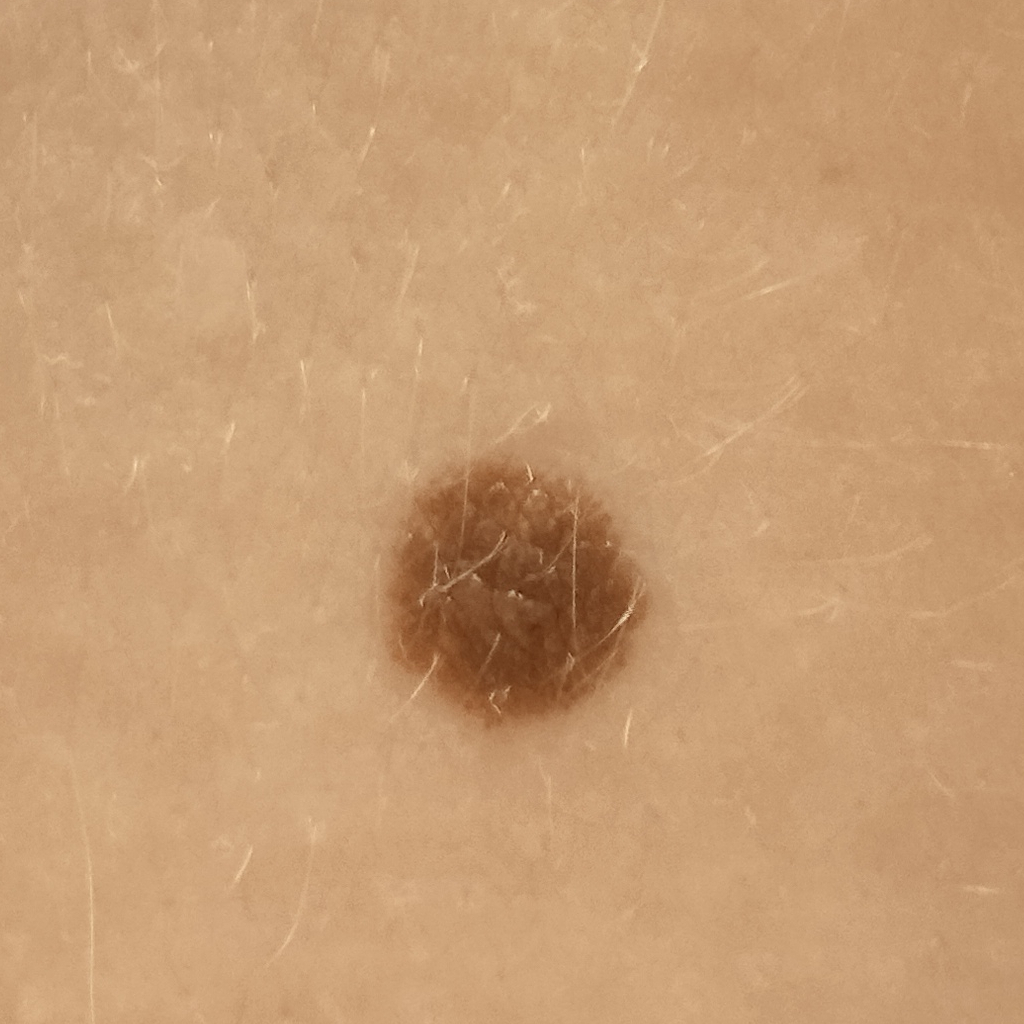risk_factors:
  positive:
    - a history of sunbed use
referral: research study (no referral diagnosis)
sun_reaction: skin reddens with sun exposure
image: clinical photograph
lesion_size:
  diameter_mm: 9.1
diagnosis:
  name: melanocytic nevus
  malignancy: benign